The chart documents a prior melanoma. A female subject in their mid- to late 50s. Contact-polarized dermoscopy of a skin lesion. The patient was assessed as Fitzpatrick skin type I.
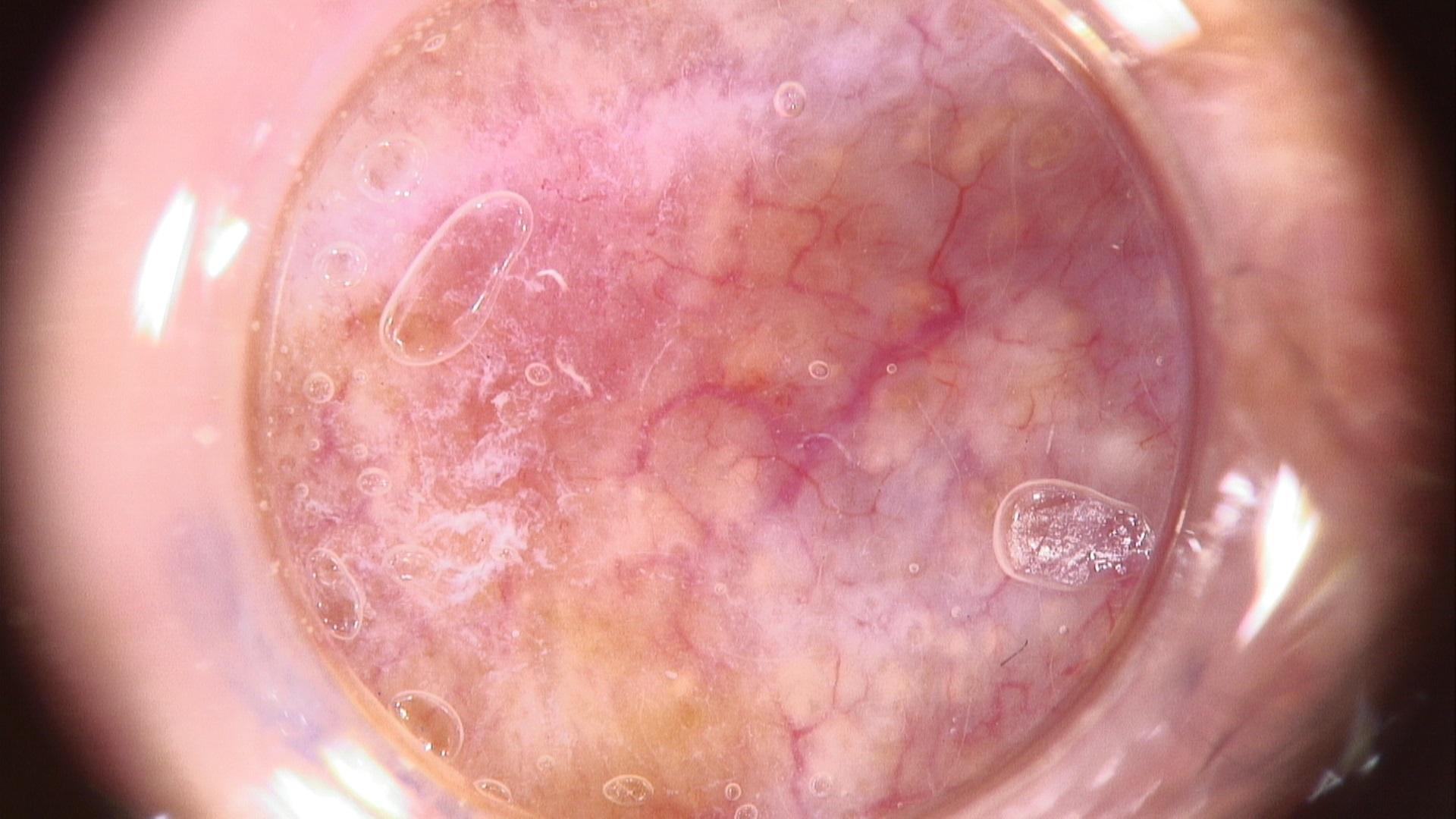Clinical context:
The lesion is located on the head or neck.
Diagnosis:
Confirmed on histopathology as a tumor of follicular differentiation — a basal cell carcinoma.